Collected as part of a research study, without a referral diagnosis; a clinical close-up of a skin lesion; the patient describes having a moderate number of moles; on a questionnaire the patient reported a personal history of cancer, a personal history of skin cancer, and no prior organ transplant; a male subject 77 years of age; the patient says their skin reddens with sun exposure — 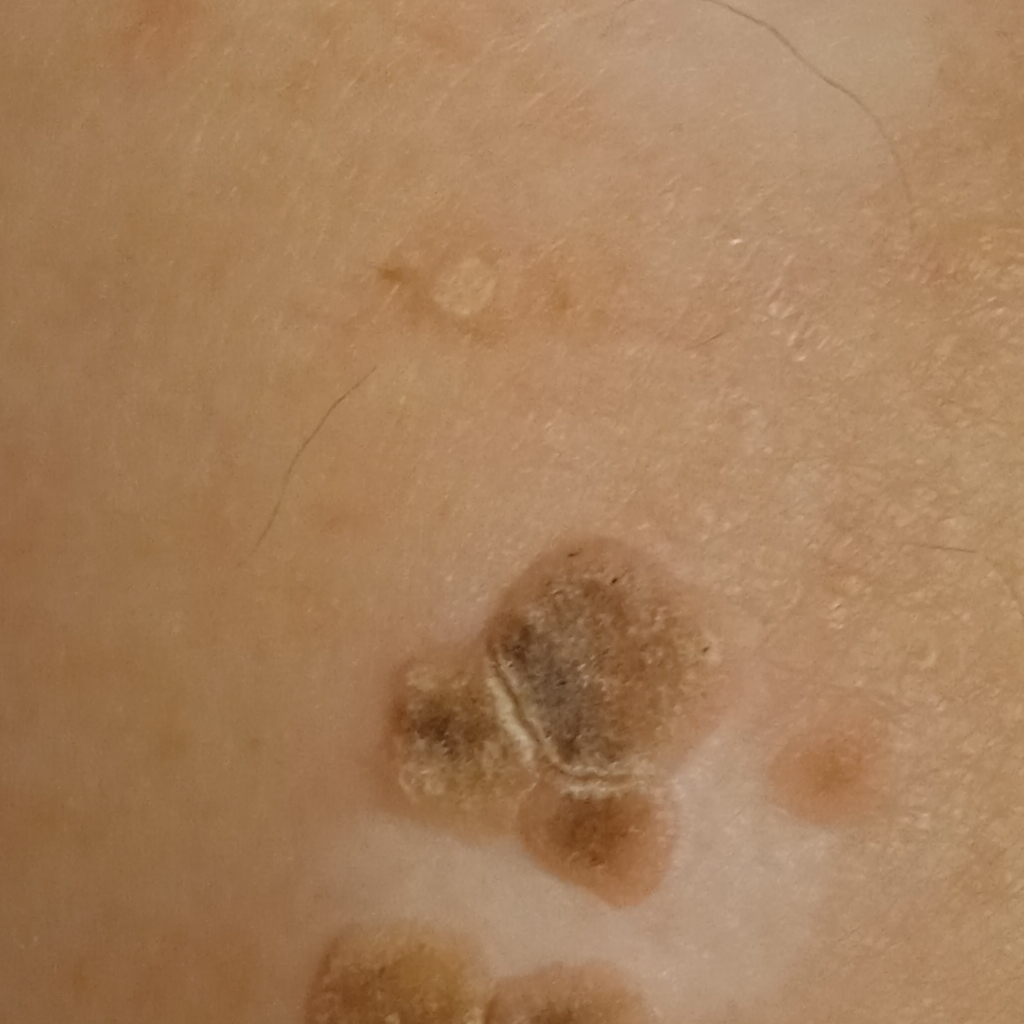The lesion involves the back.
The lesion measures approximately 14.2 mm.
Dermatologist review favored a seborrheic keratosis.